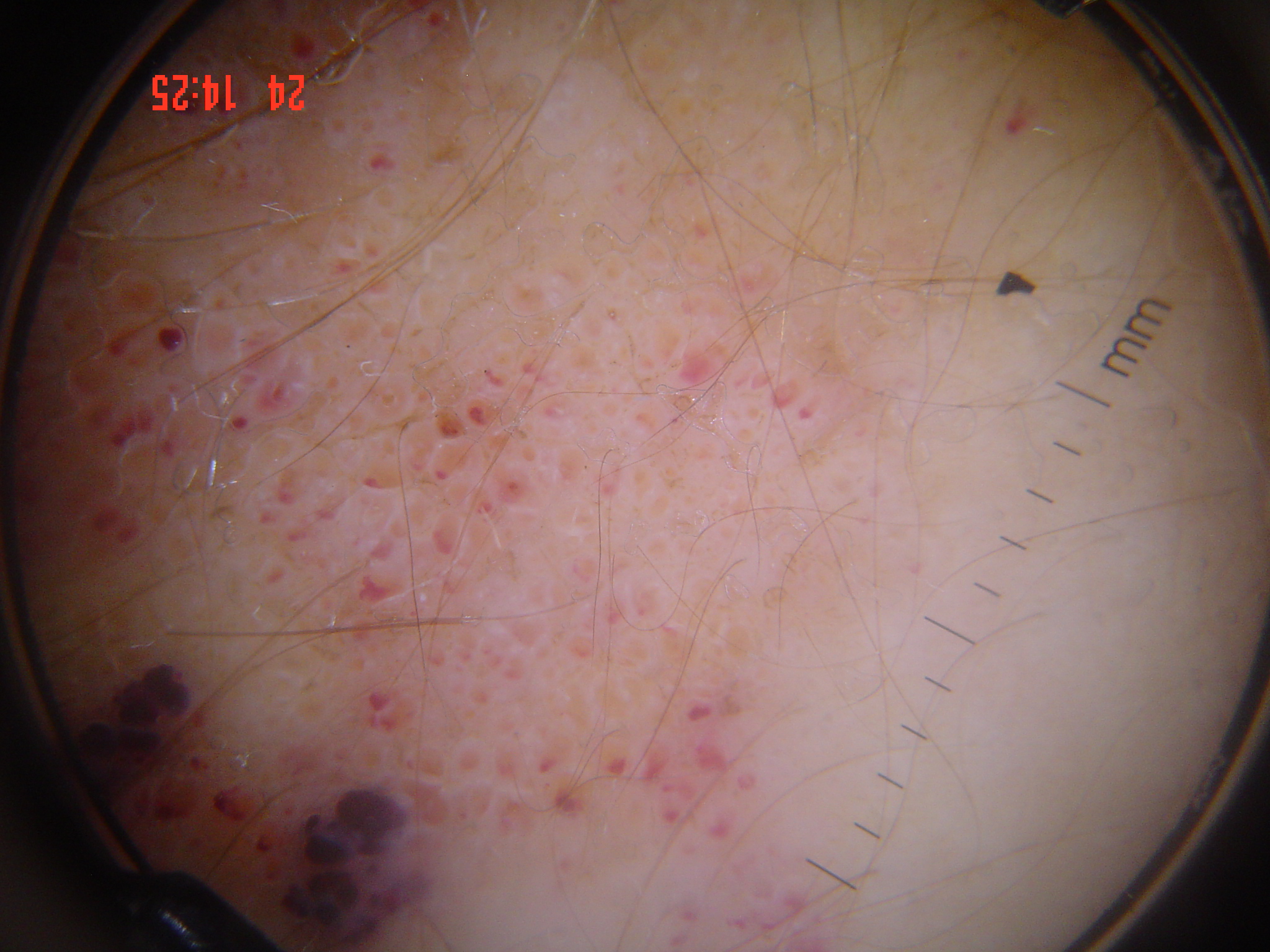Case:
– category: vascular
– label: lymphangioma (expert consensus)